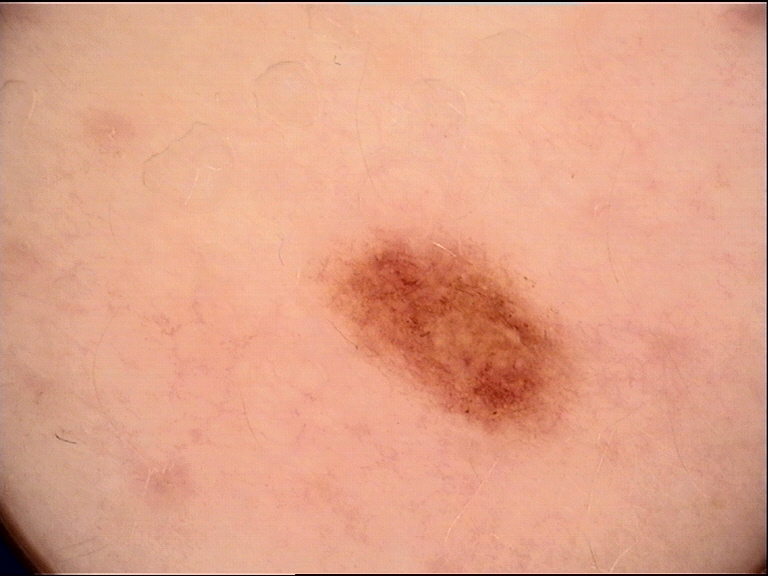<lesion>
  <diagnosis>
    <name>dysplastic junctional nevus</name>
    <code>jd</code>
    <malignancy>benign</malignancy>
    <super_class>melanocytic</super_class>
    <confirmation>expert consensus</confirmation>
  </diagnosis>
</lesion>